A dermoscopic photograph of a skin lesion.
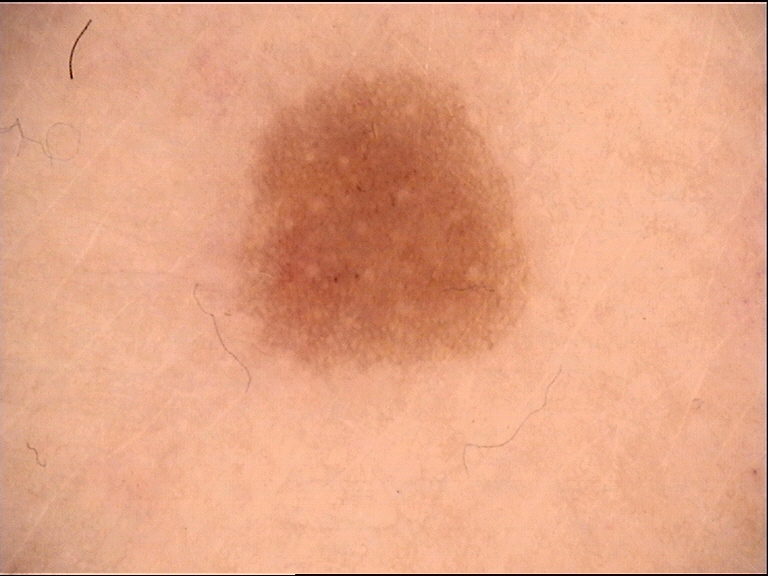Diagnosed as a benign lesion — an acral dysplastic junctional nevus.